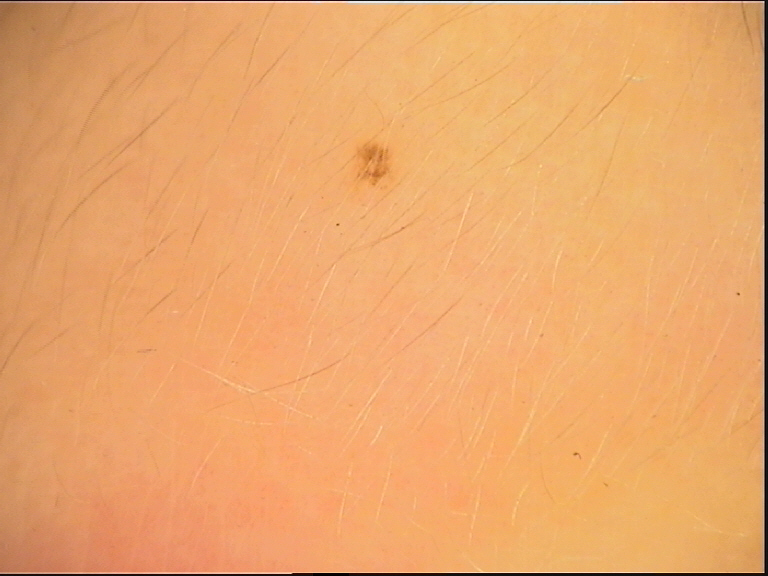A skin lesion imaged with a dermatoscope.
The diagnostic label was a compound lesion — a Miescher nevus.